A dermoscopic image of a skin lesion:
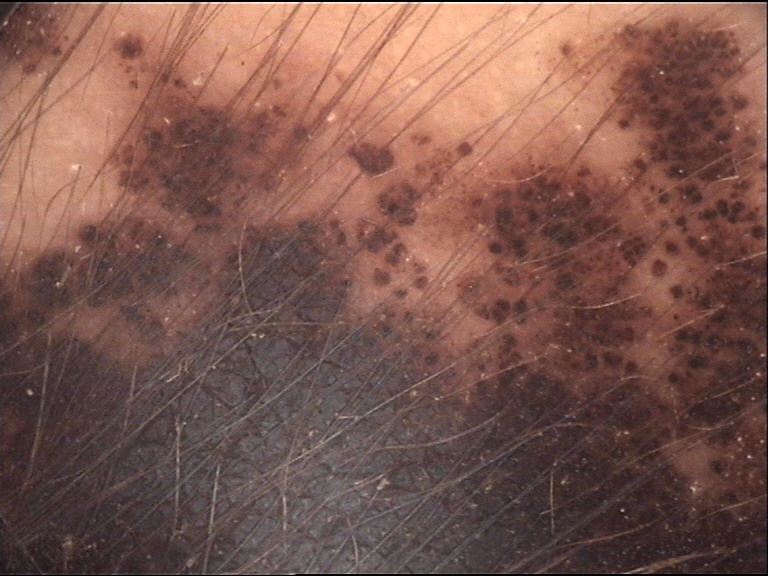This is a banal lesion. The diagnostic label was a congenital compound nevus.